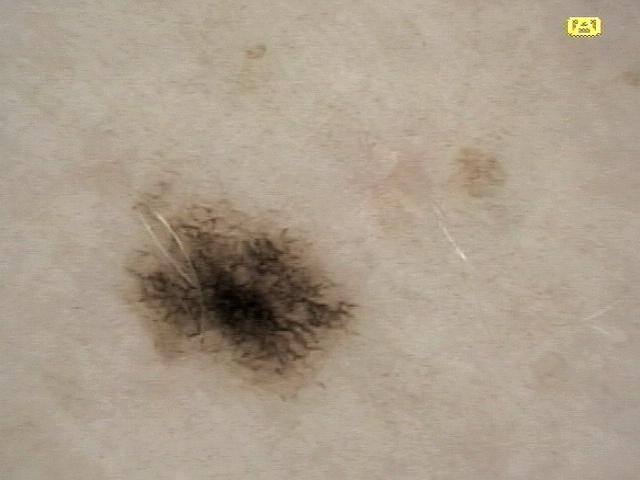Clinical context:
A dermoscopic image of a skin lesion. The lesion was found on the anterior trunk.
Conclusion:
The biopsy diagnosis was a nevus.